A dermoscopic close-up of a skin lesion: 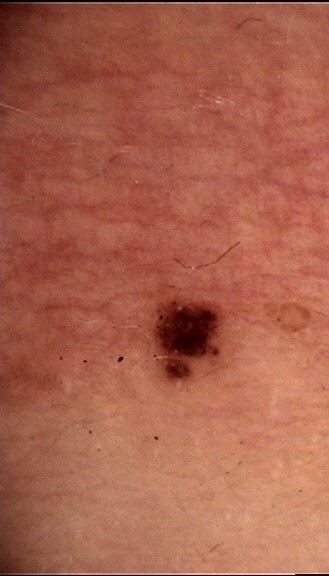Diagnosed as a dysplastic junctional nevus.